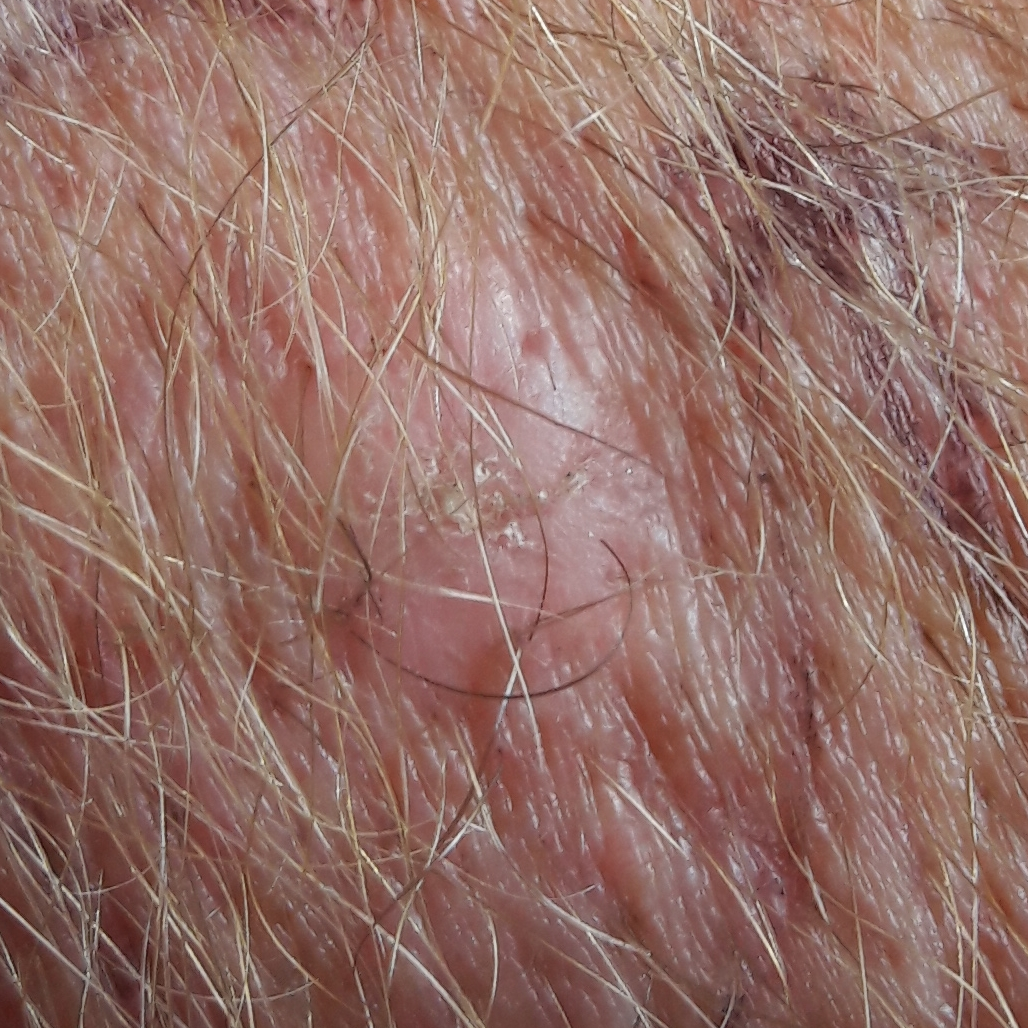<case>
<skin_type>III</skin_type>
<patient>
<age>45</age>
<gender>male</gender>
</patient>
<image>clinical photograph</image>
<risk_factors>
<positive>prior skin cancer (patient or family), prior cancer (patient or family), pesticide exposure</positive>
</risk_factors>
<lesion_location>a forearm</lesion_location>
<lesion_size>
<diameter_1_mm>10.0</diameter_1_mm>
<diameter_2_mm>10.0</diameter_2_mm>
</lesion_size>
<symptoms>
<present>elevation, growth, itching</present>
<absent>pain, bleeding</absent>
</symptoms>
<diagnosis>
<name>actinic keratosis</name>
<code>ACK</code>
<malignancy>indeterminate</malignancy>
<confirmation>histopathology</confirmation>
</diagnosis>
</case>